Acquired for a research image collection, with no referral diagnosis. The patient says their skin reddens with sun exposure. A male subject aged 76. By self-report, a personal history of skin cancer, a personal history of cancer, no prior organ transplant, and no sunbed use. Dermoscopy of a skin lesion. Few moles overall by the patient's own estimate:
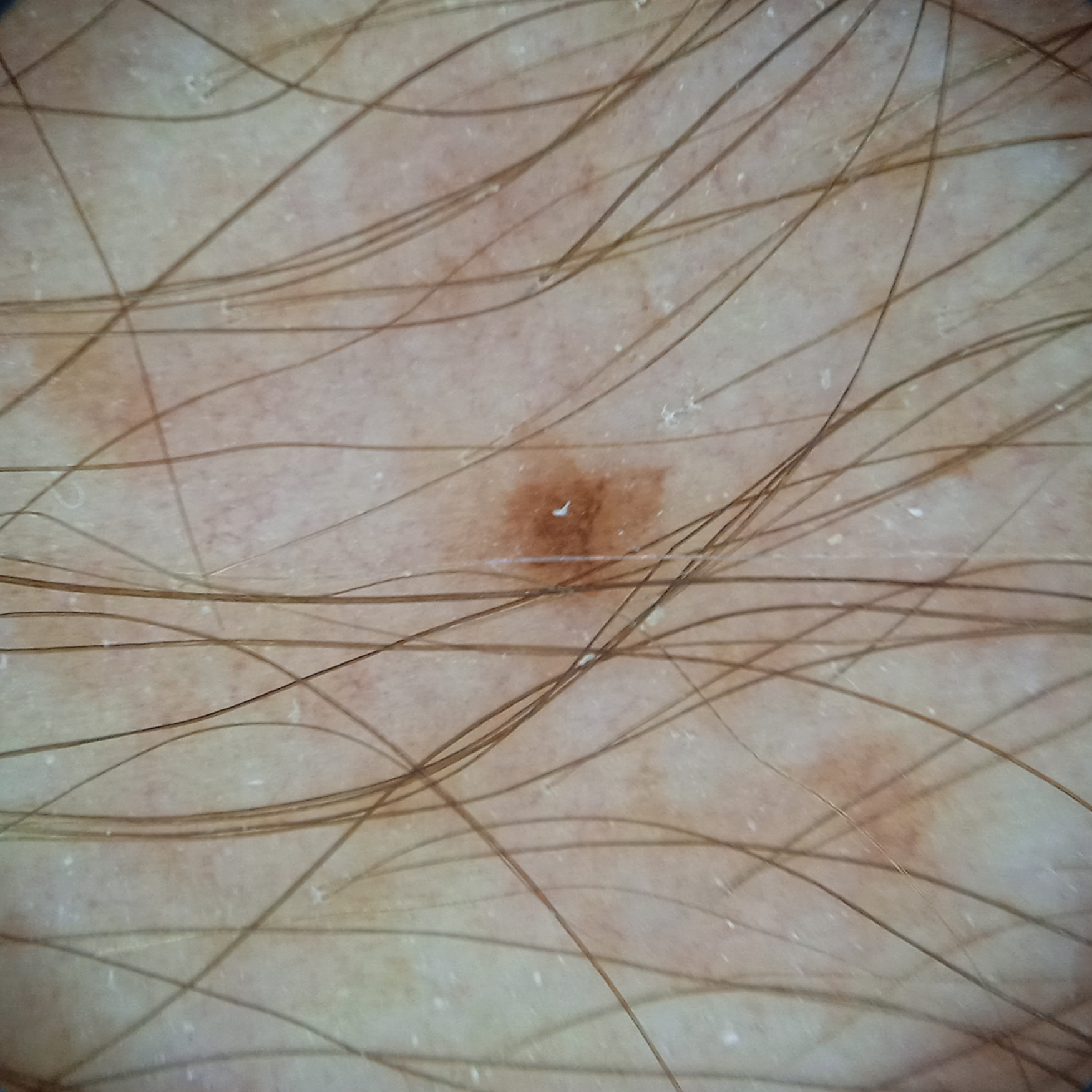Findings:
* anatomic site · an arm
* lesion size · 8.2 mm
* assessment · melanocytic nevus (dermatologist consensus)